This is a dermoscopic photograph of a skin lesion: 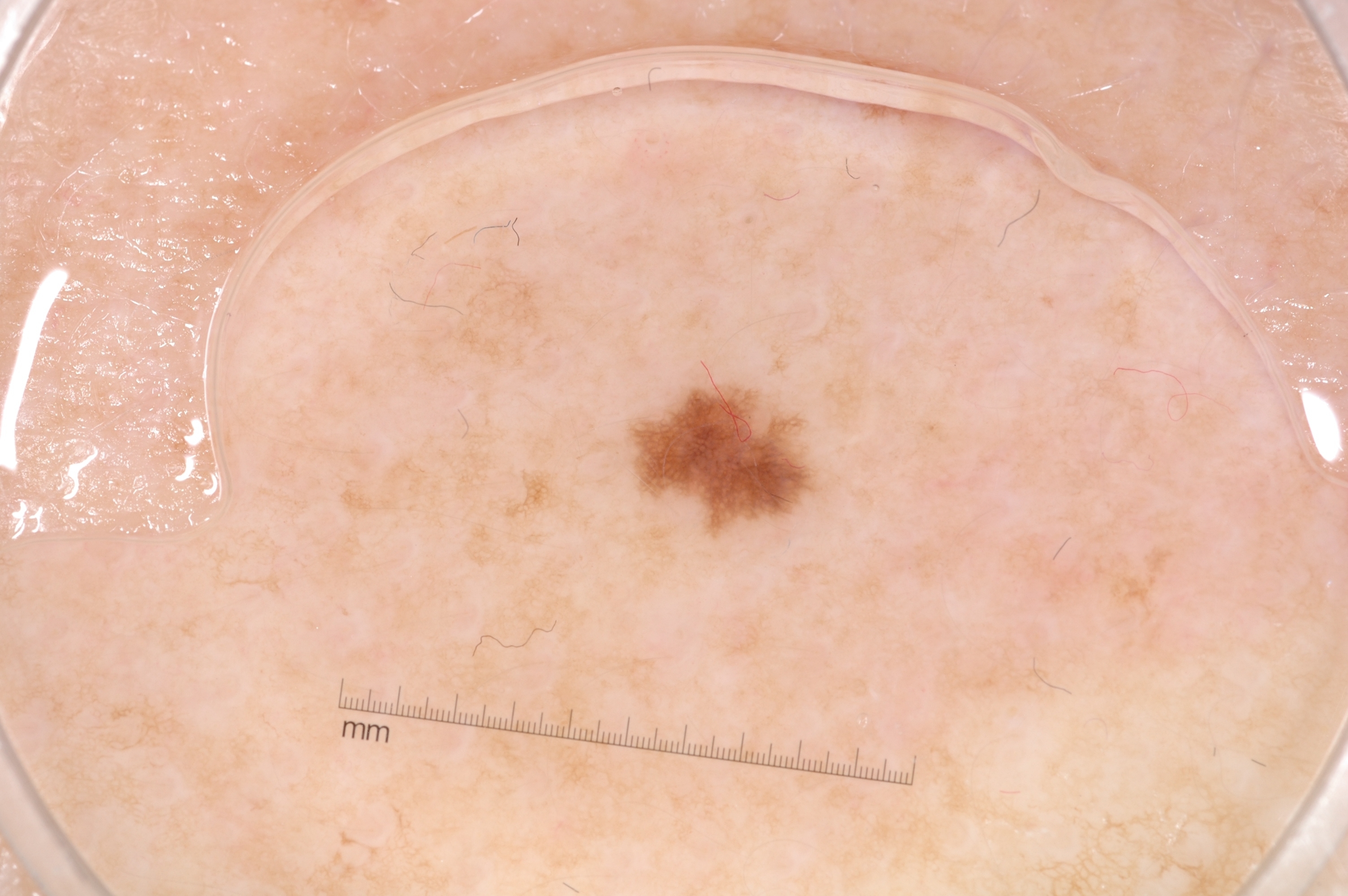With coordinates (x1, y1, x2, y2), the lesion's extent is [643, 385, 811, 518]. Diagnosed as a melanocytic nevus.